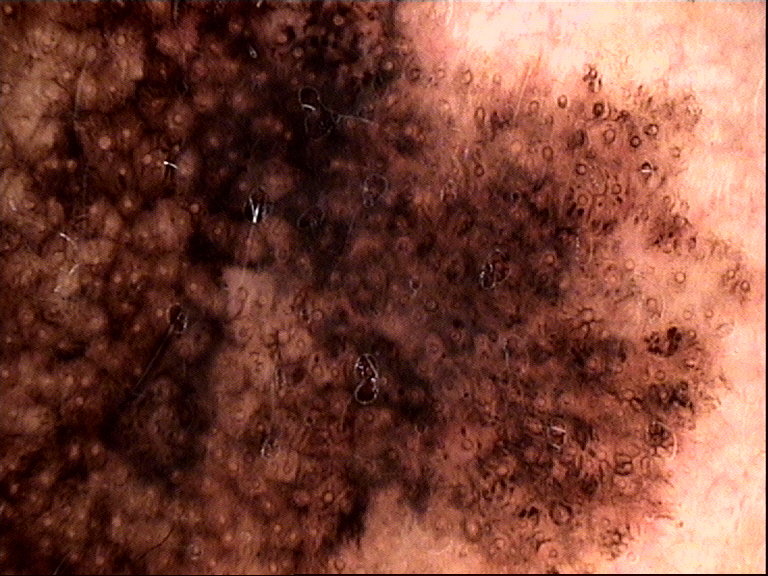label=lentigo maligna (biopsy-proven).